No relevant systemic symptoms · present for less than one week · the patient indicates the lesion is raised or bumpy · the patient considered this a rash · the lesion is associated with itching · skin tone: Fitzpatrick V; lay reviewers estimated MST 7 (US pool) or 6 (India pool) · the back of the hand is involved · the photo was captured at an angle: 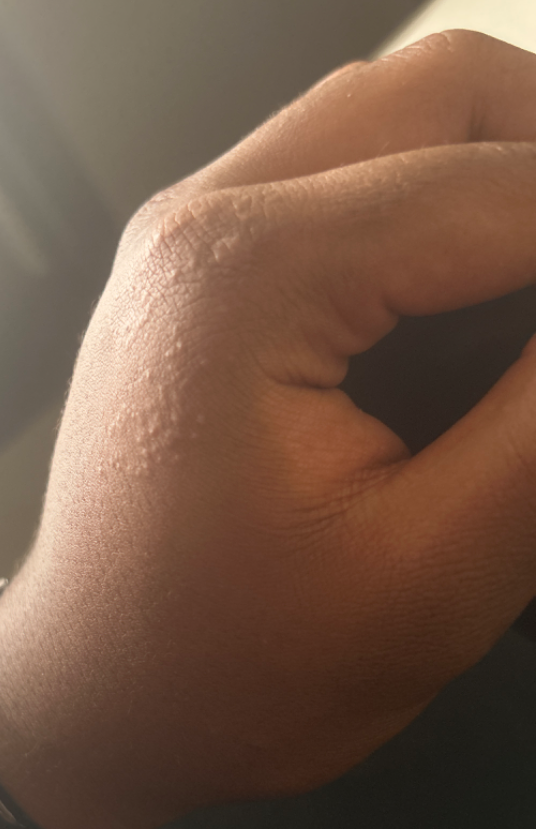  assessment: could not be assessed